The subject is a male in their 70s; a dermoscopic image of a skin lesion:
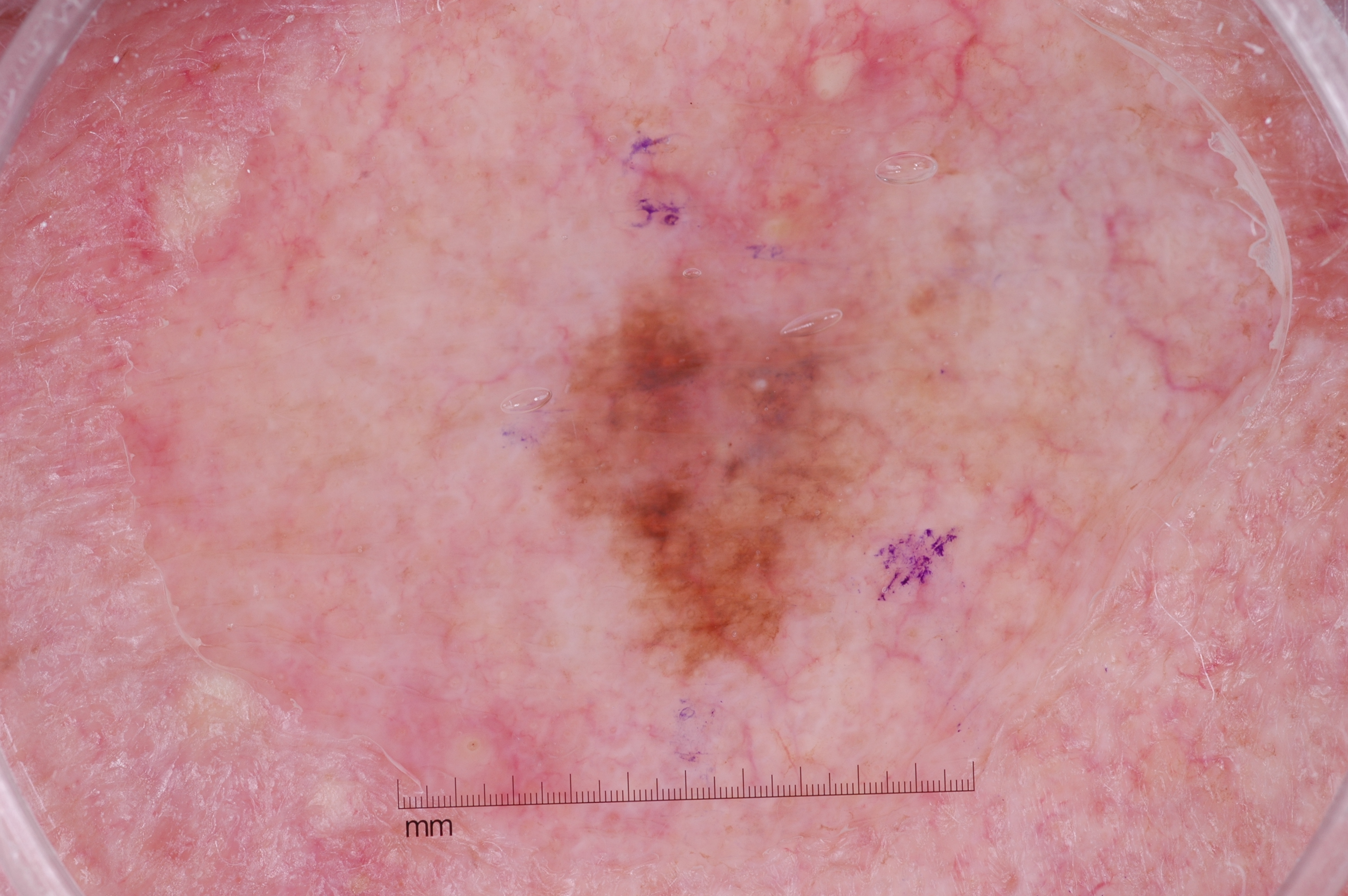Q: What does dermoscopy show?
A: milia-like cysts; absent: negative network, pigment network, and streaks
Q: Where is the lesion in the image?
A: 548/280/863/665
Q: How large is the lesion within the image?
A: ~7% of the field
Q: What is the diagnosis?
A: a melanoma, a skin cancer